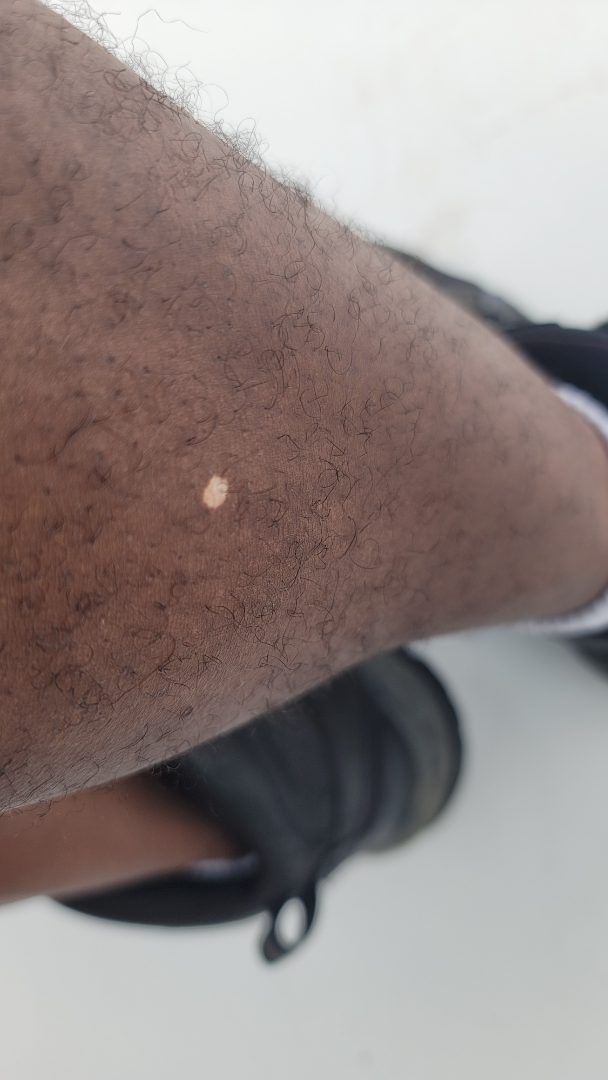No differential diagnosis could be assigned on photographic review.